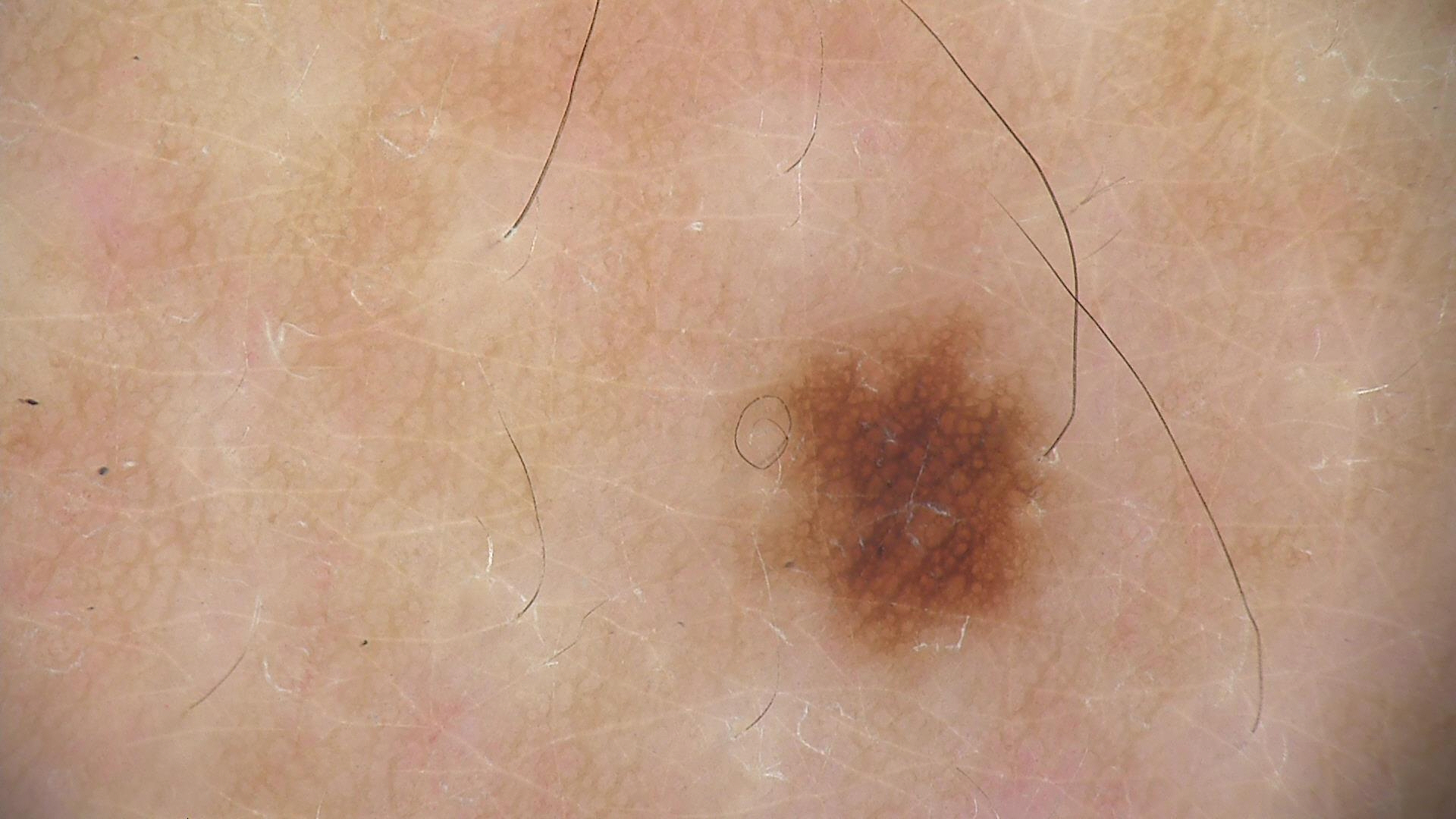Consistent with a dysplastic junctional nevus.